A skin lesion imaged with a dermatoscope; a male patient, in their mid-70s: 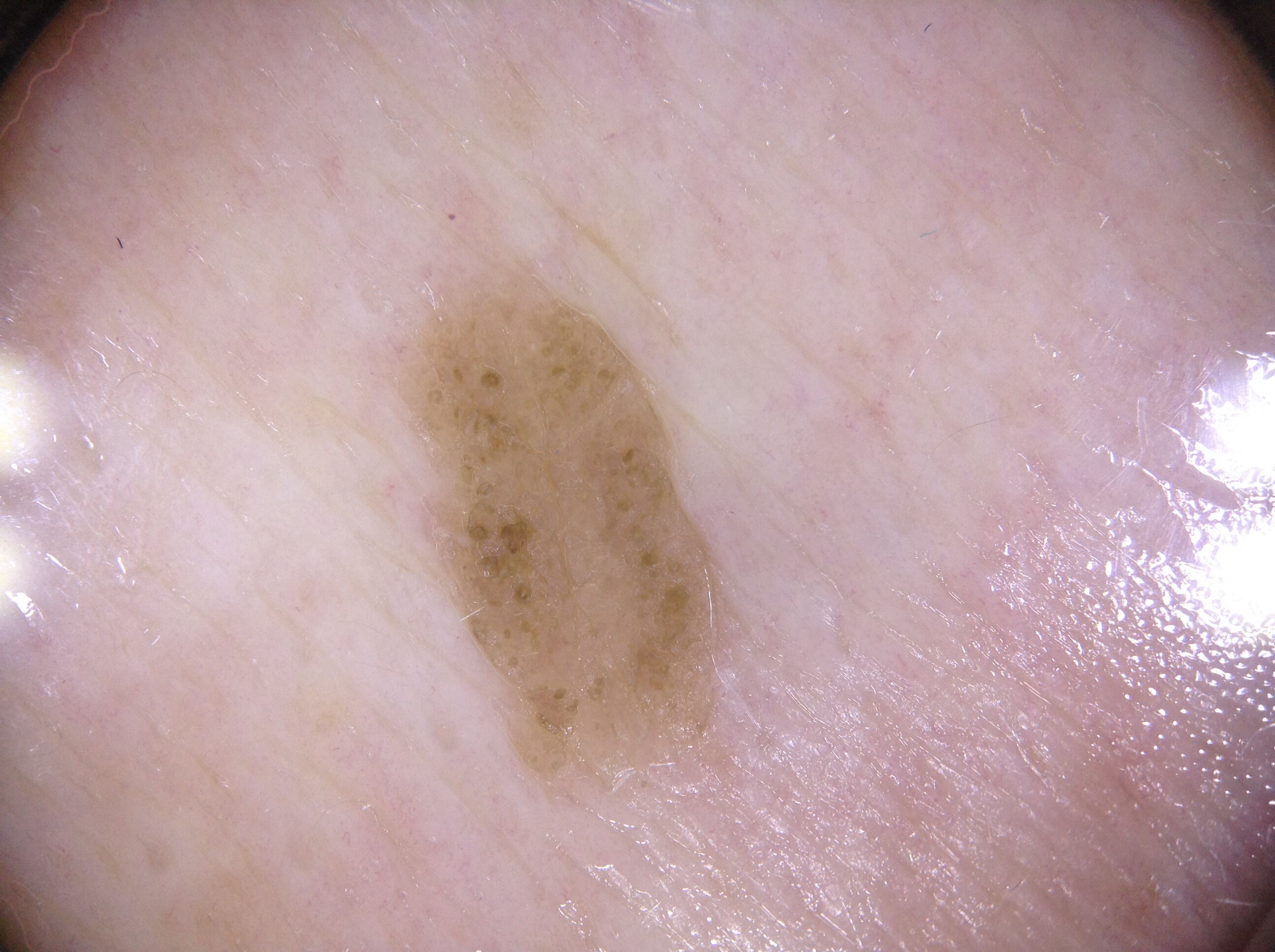location: bbox(391, 232, 774, 811)
dermoscopic features assessed but absent: streaks, negative network, pigment network, and milia-like cysts
diagnostic label: a seborrheic keratosis, a benign skin lesion